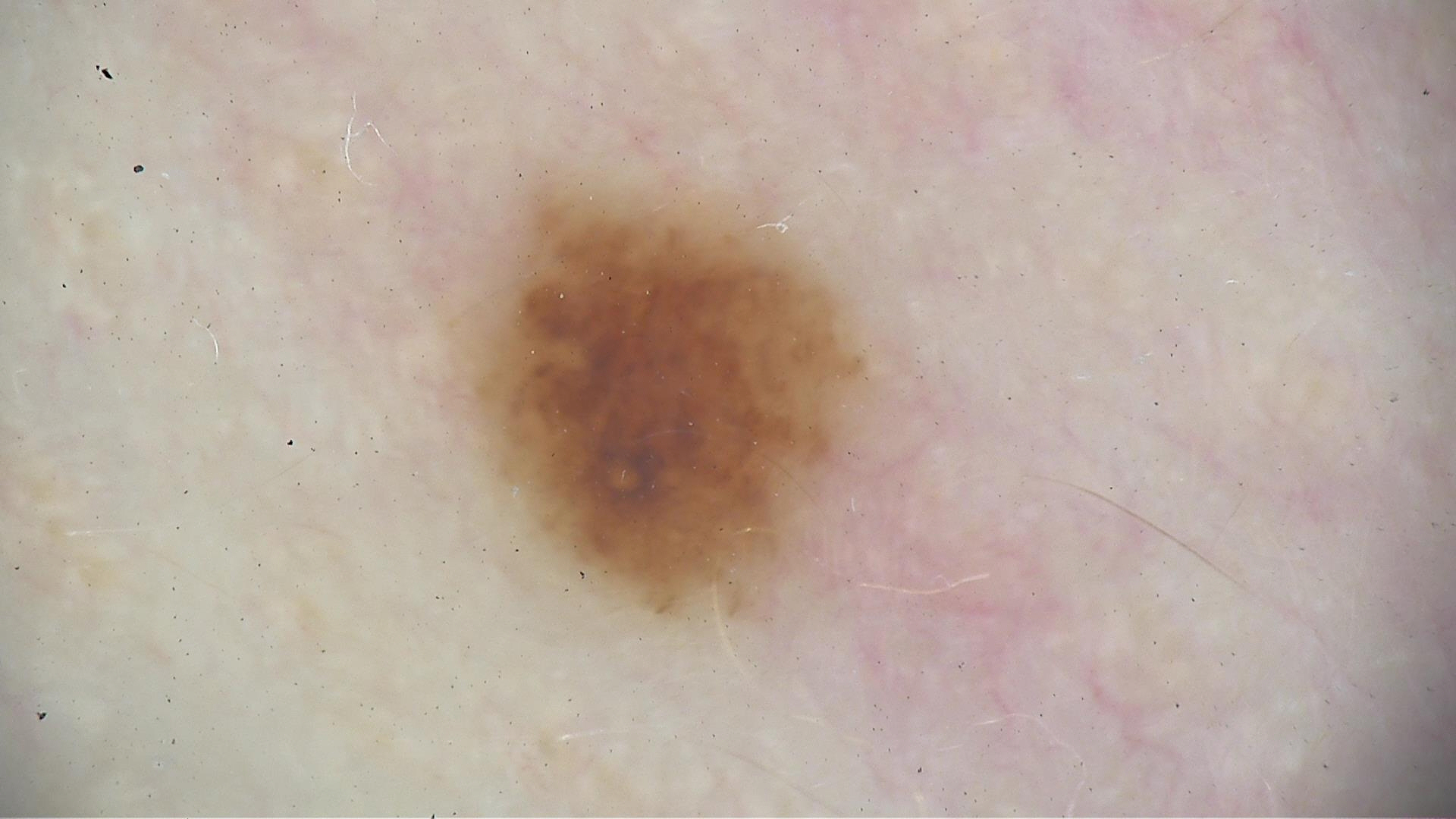Q: What was the diagnostic impression?
A: dysplastic junctional nevus (expert consensus)